The affected area is the head or neck, the contributor is a female aged 30–39, this image was taken at an angle: 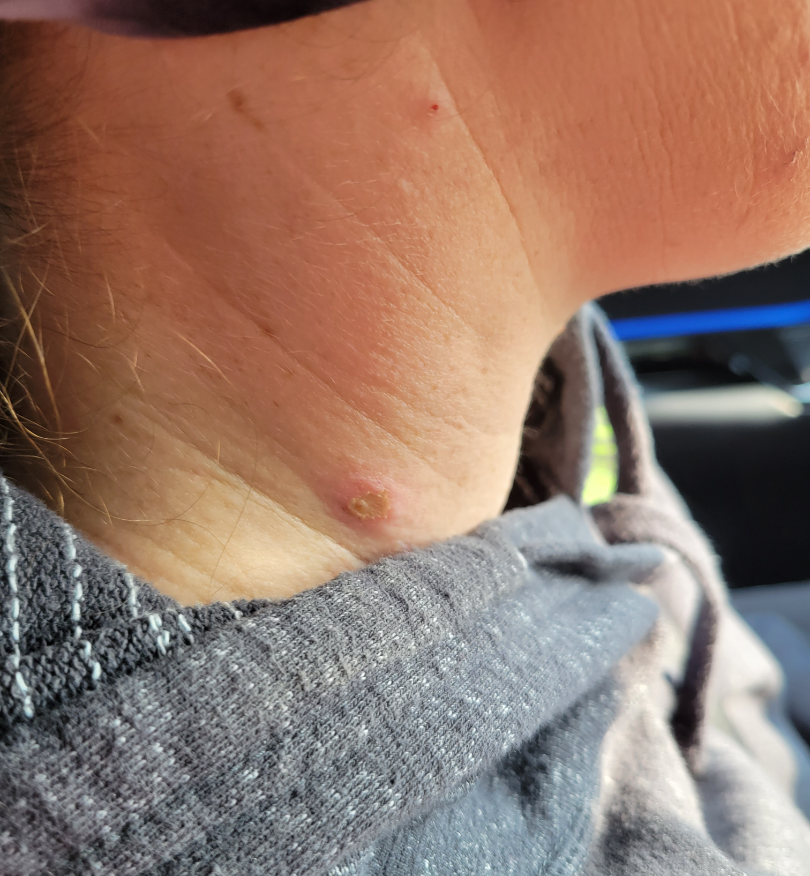Q: What was the assessment?
A: indeterminate